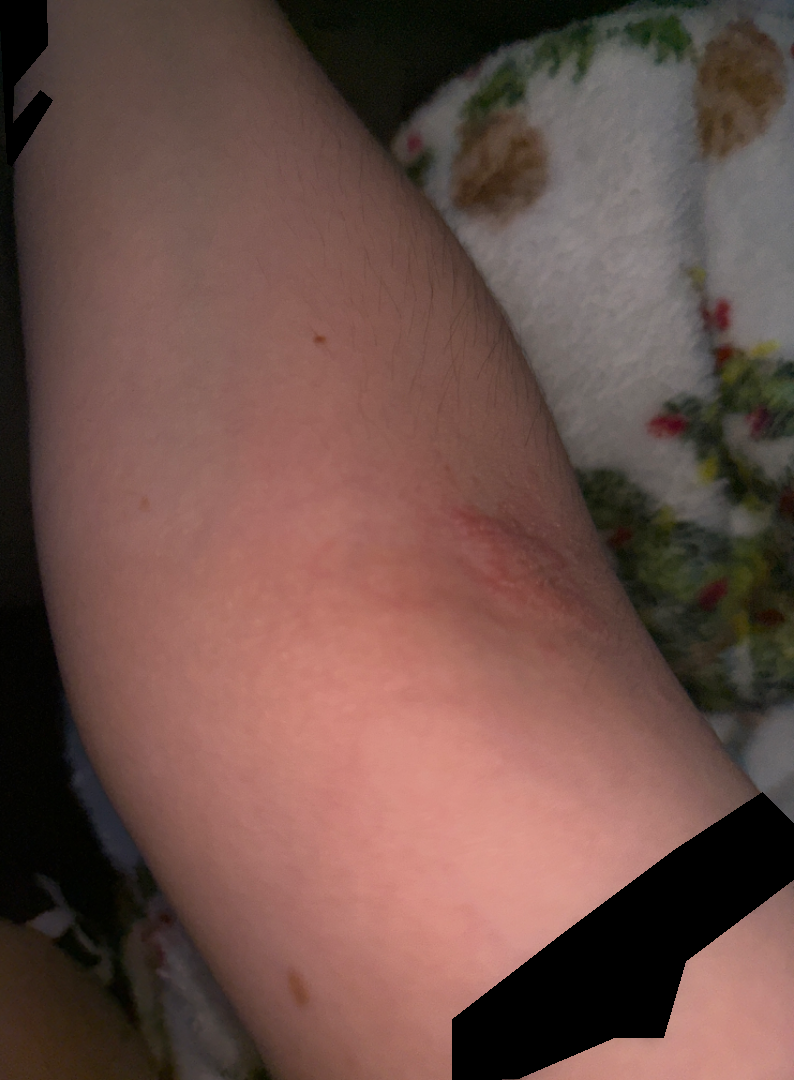An image taken at an angle.
FST III; human graders estimated a MST of 2.
On dermatologist assessment of the image: Eczema (favored).